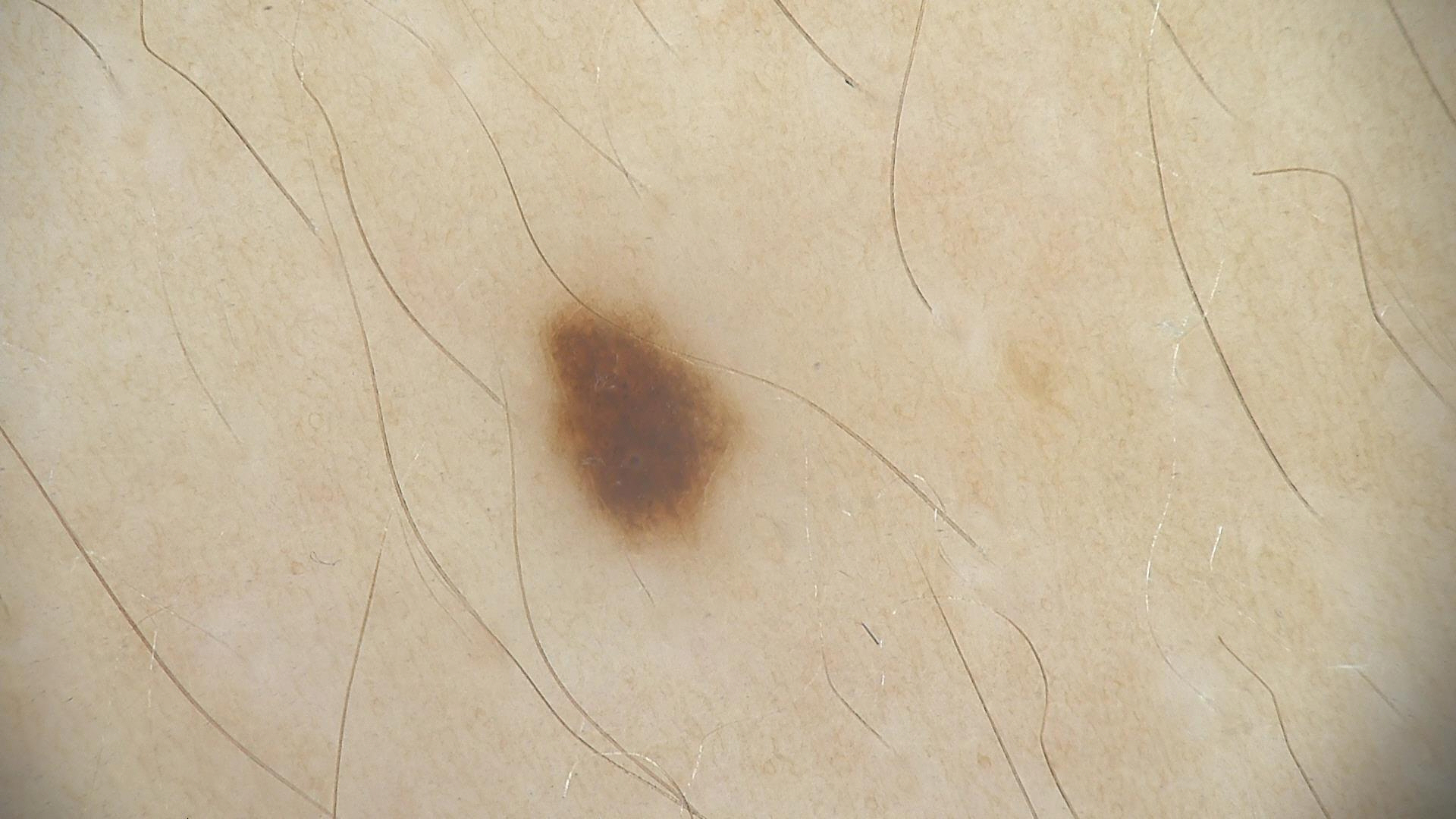Case:
• image type · dermoscopy
• diagnosis · dysplastic junctional nevus (expert consensus)